Located on the front of the torso, leg, back of the hand, head or neck, arm and palm · the photograph was taken at an angle:
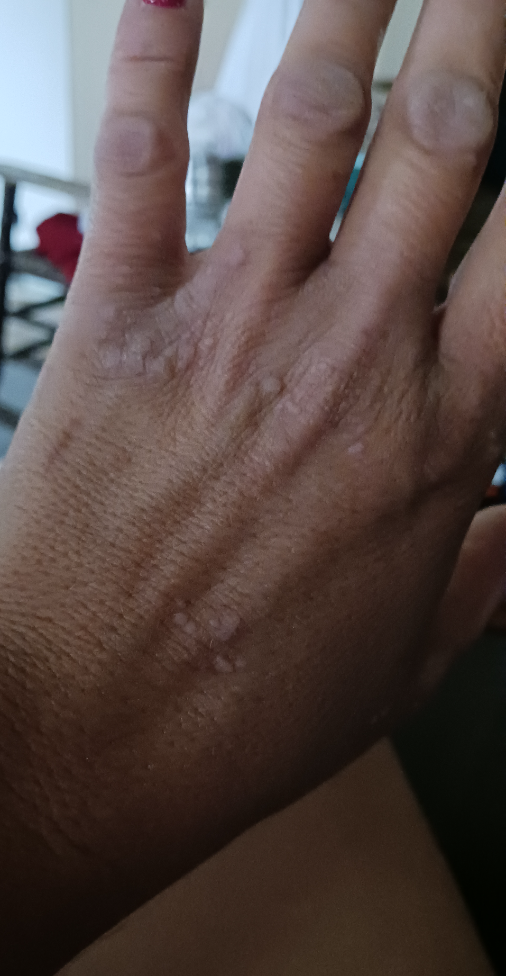{
  "differential": {
    "leading": [
      "Verruca vulgaris"
    ],
    "considered": [
      "Lichen planus/lichenoid eruption"
    ]
  }
}